A close-up photograph · the lesion involves the leg, head or neck and arm · the lesion is described as raised or bumpy and fluid-filled · reported duration is one to four weeks · symptoms reported: bleeding, burning, itching, bothersome appearance and pain:
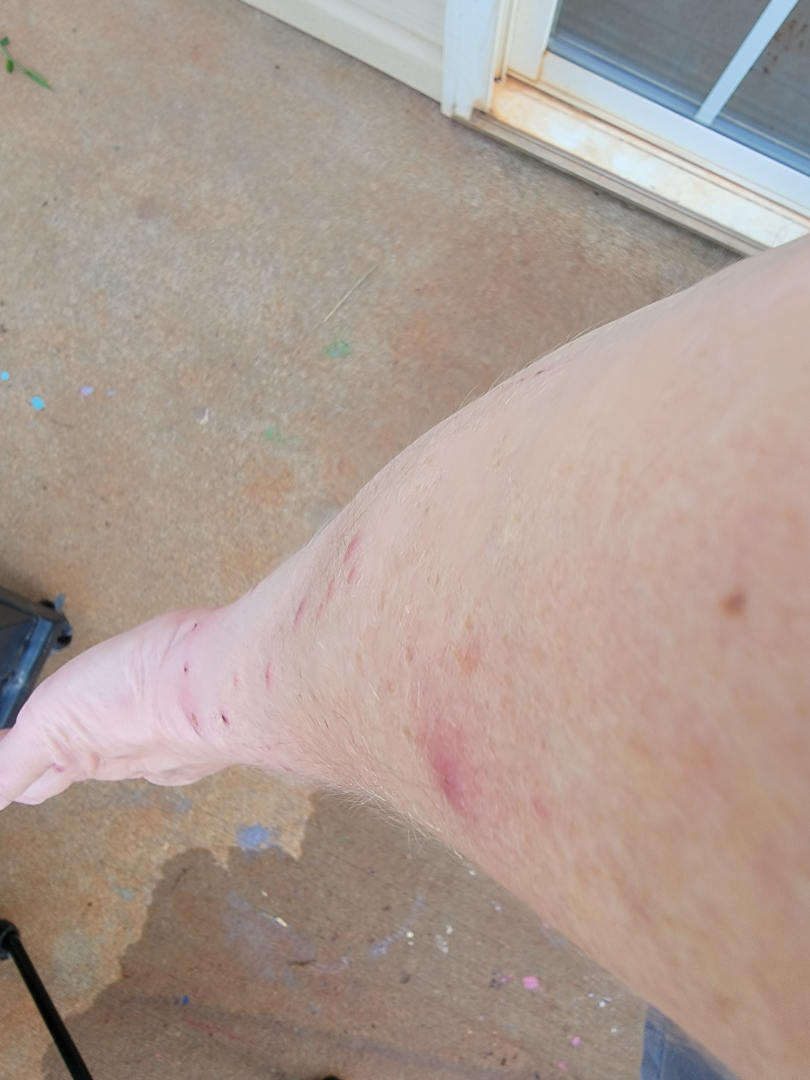assessment — ungradable on photographic review